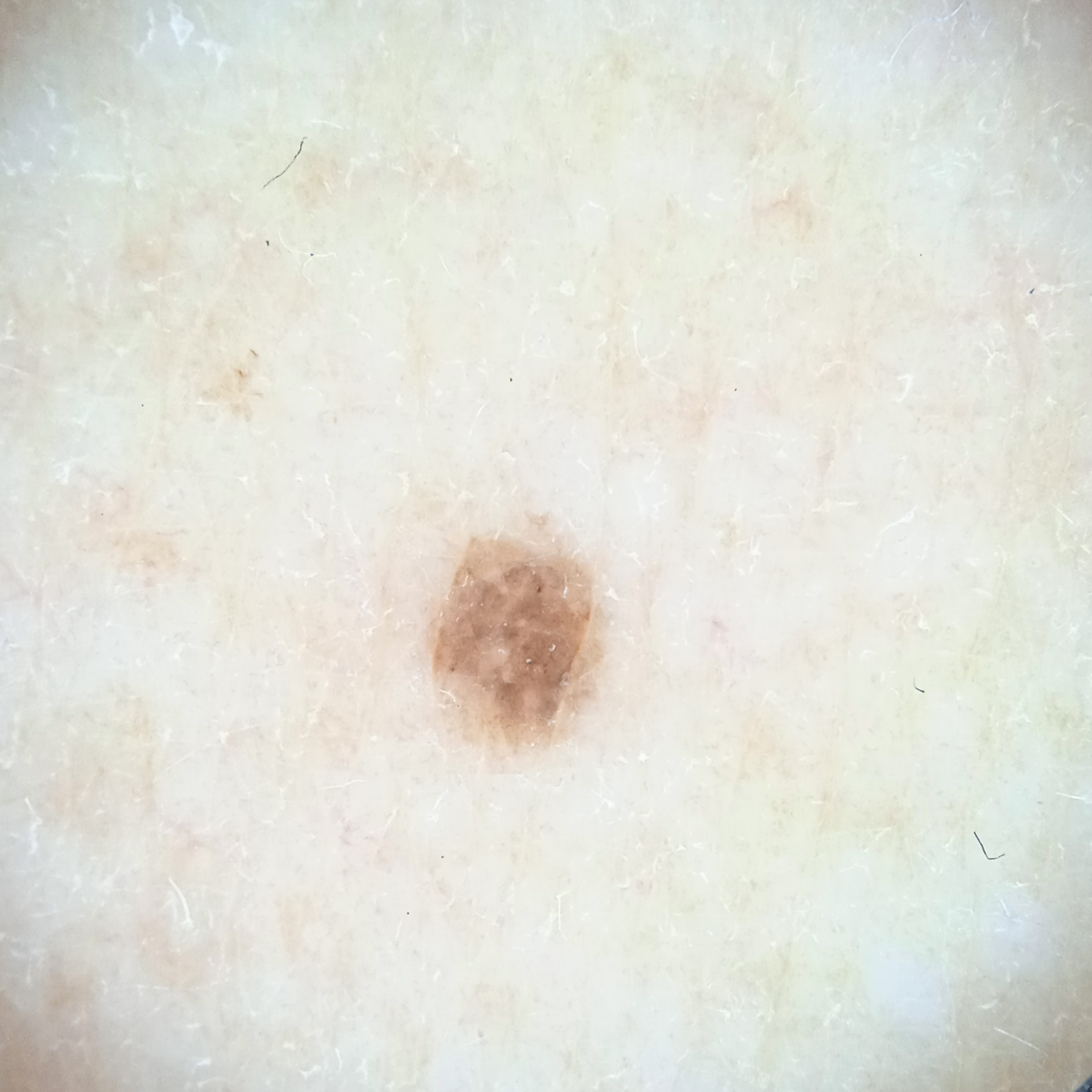patient: female, 50 years of age; nevus count: a moderate number of melanocytic nevi; risk factors: a personal history of skin cancer, no immunosuppression, no family history of skin cancer; referral: research study (no referral diagnosis); sun reaction: skin reddens with sun exposure; modality: dermoscopic image; anatomic site: an arm; diameter: 2.5 mm; diagnosis: melanocytic nevus (dermatologist consensus).